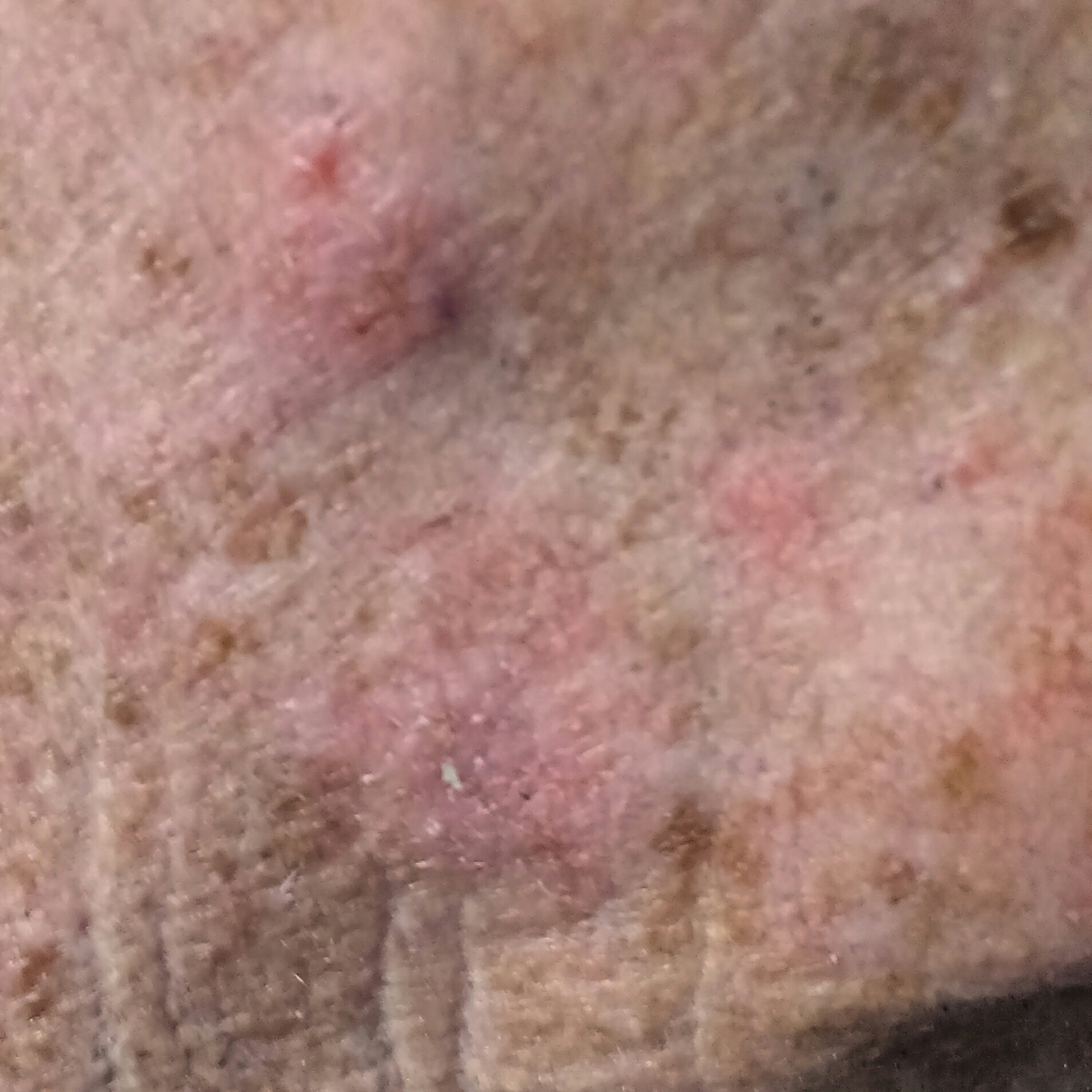subject = in their 60s; image = smartphone clinical photo; anatomic site = the face; patient-reported symptoms = elevation, itching; diagnosis = actinic keratosis (clinical consensus).